Present for about one day · this is a close-up image.
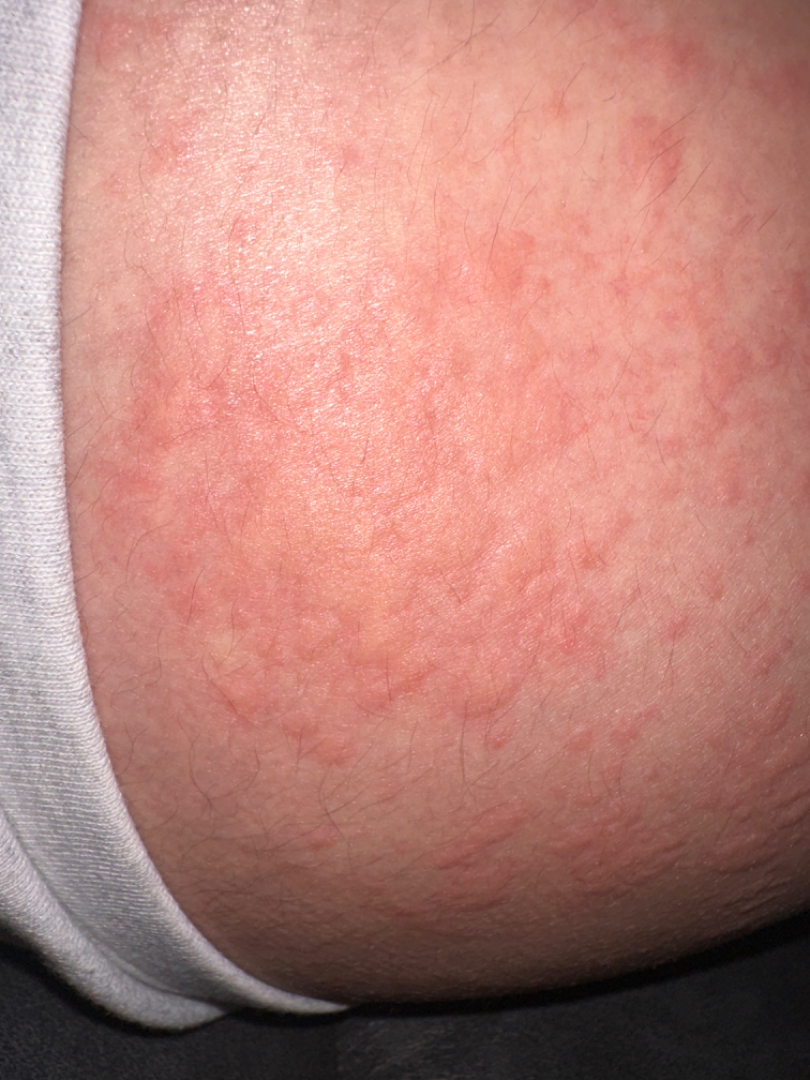clinical impression=Urticaria (weight 1.00).